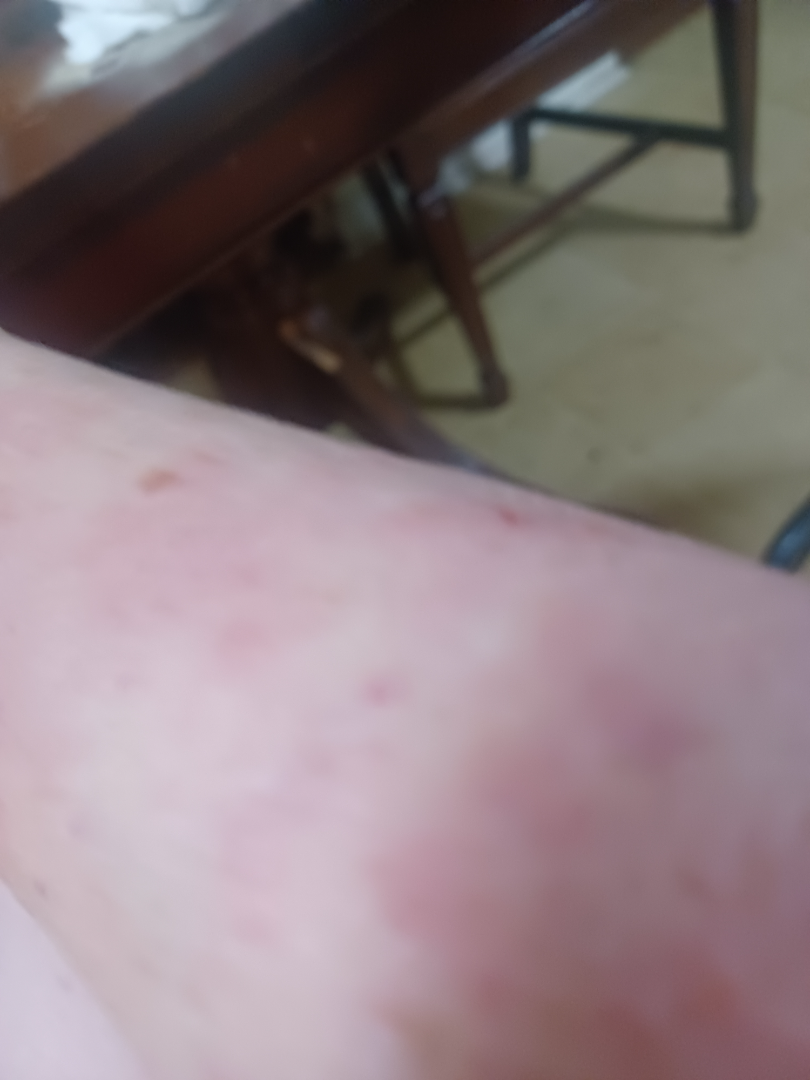The skin findings could not be characterized from the image. A close-up photograph. The affected area is the back of the hand, arm and leg.